A dermoscopic photograph of a skin lesion: 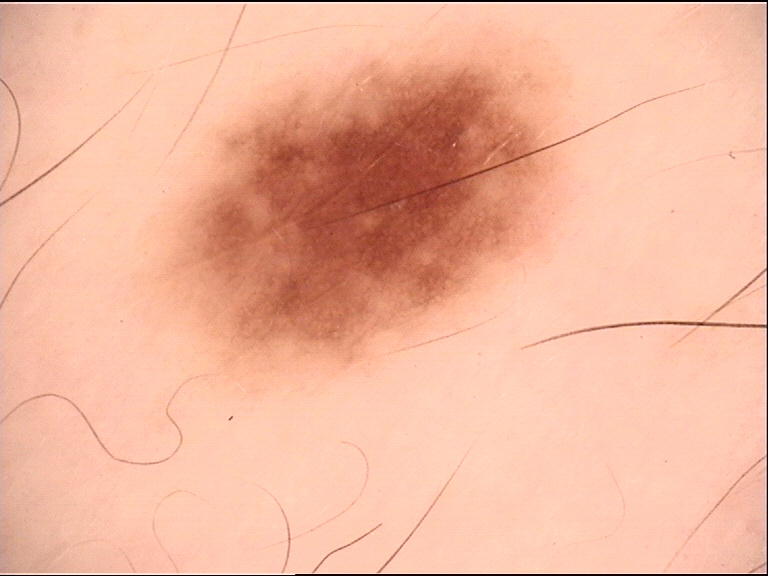Impression:
The diagnosis was a benign lesion — a dysplastic junctional nevus.